Female contributor, age 18–29. The leg and arm are involved. The photo was captured at an angle: 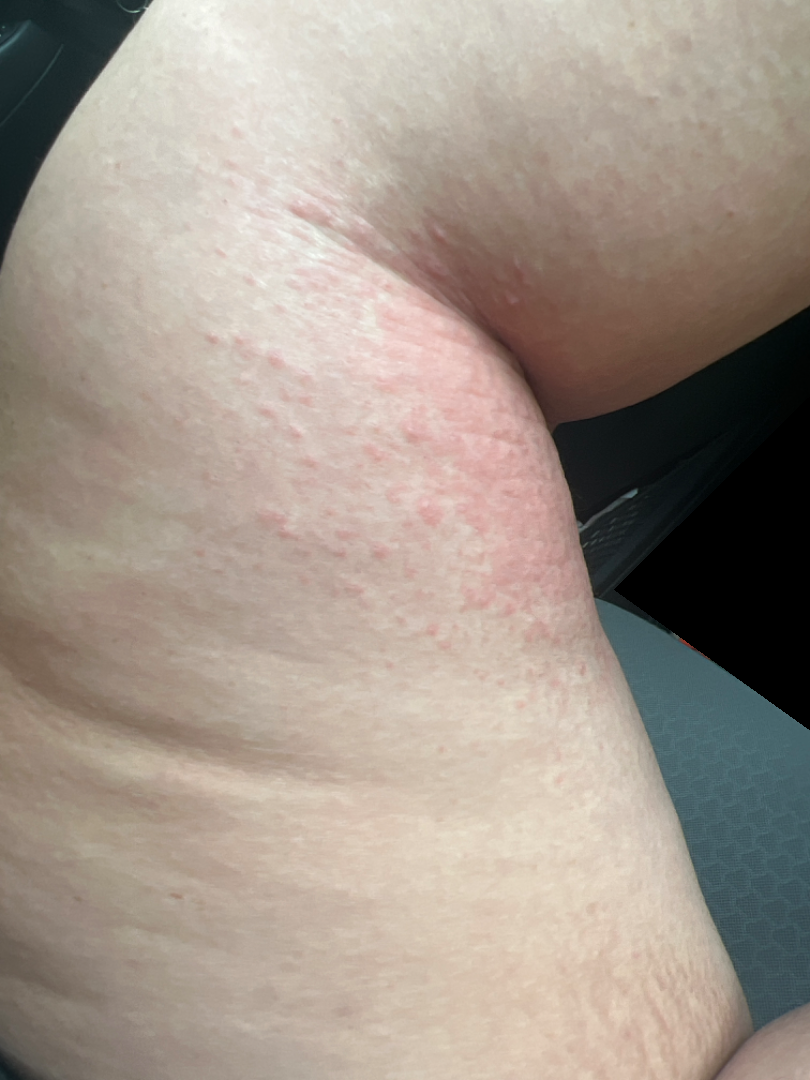Case summary:
• assessment · not assessable